A dermoscopic photograph of a skin lesion.
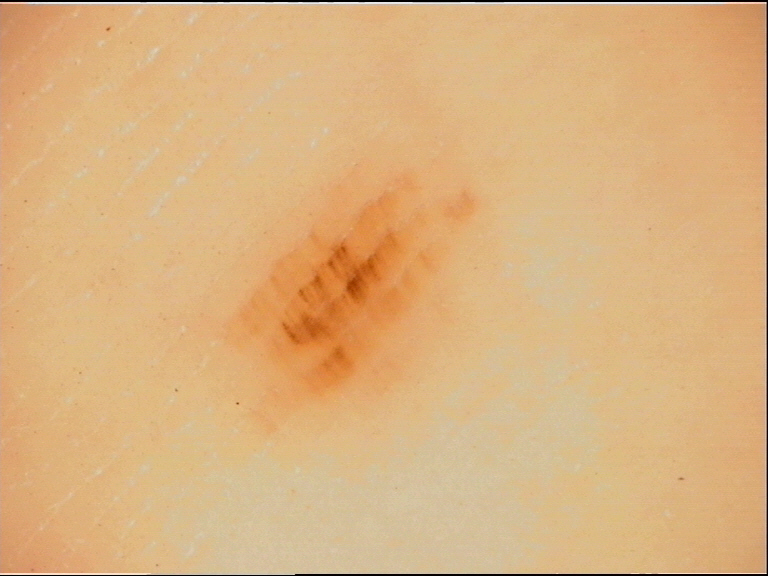The morphology is that of a banal lesion.
The diagnostic label was an acral junctional nevus.